A male subject in their mid- to late 70s — 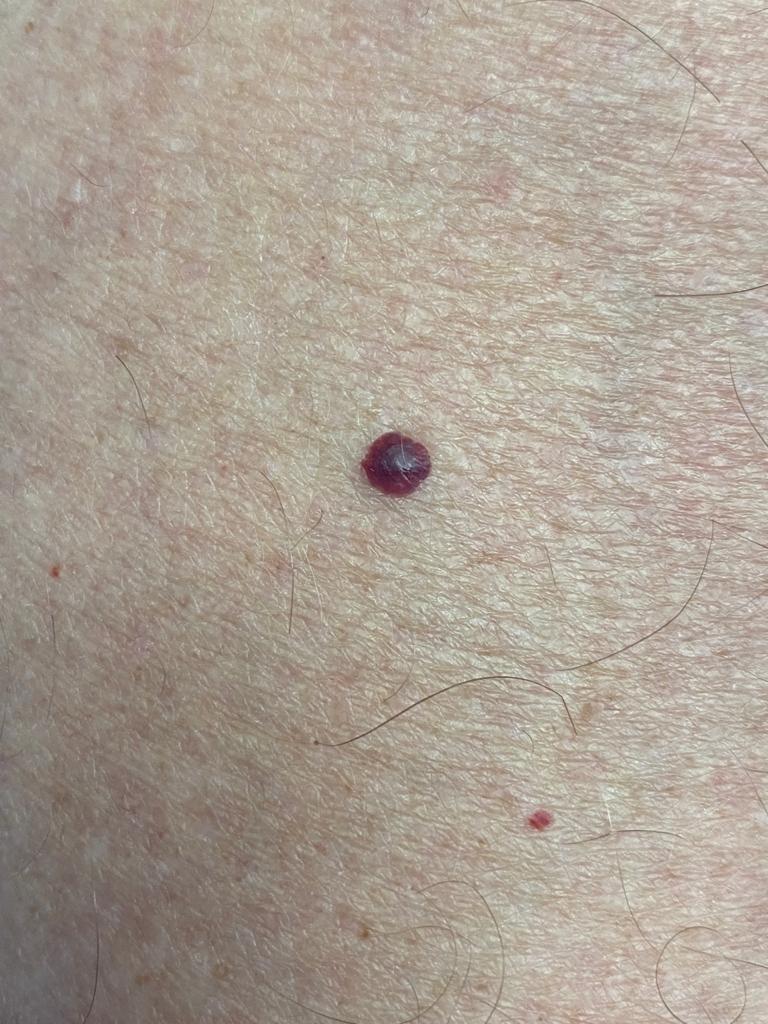Q: Where on the body is the lesion?
A: the trunk
Q: What is this lesion?
A: vascular lesion (clinical impression)